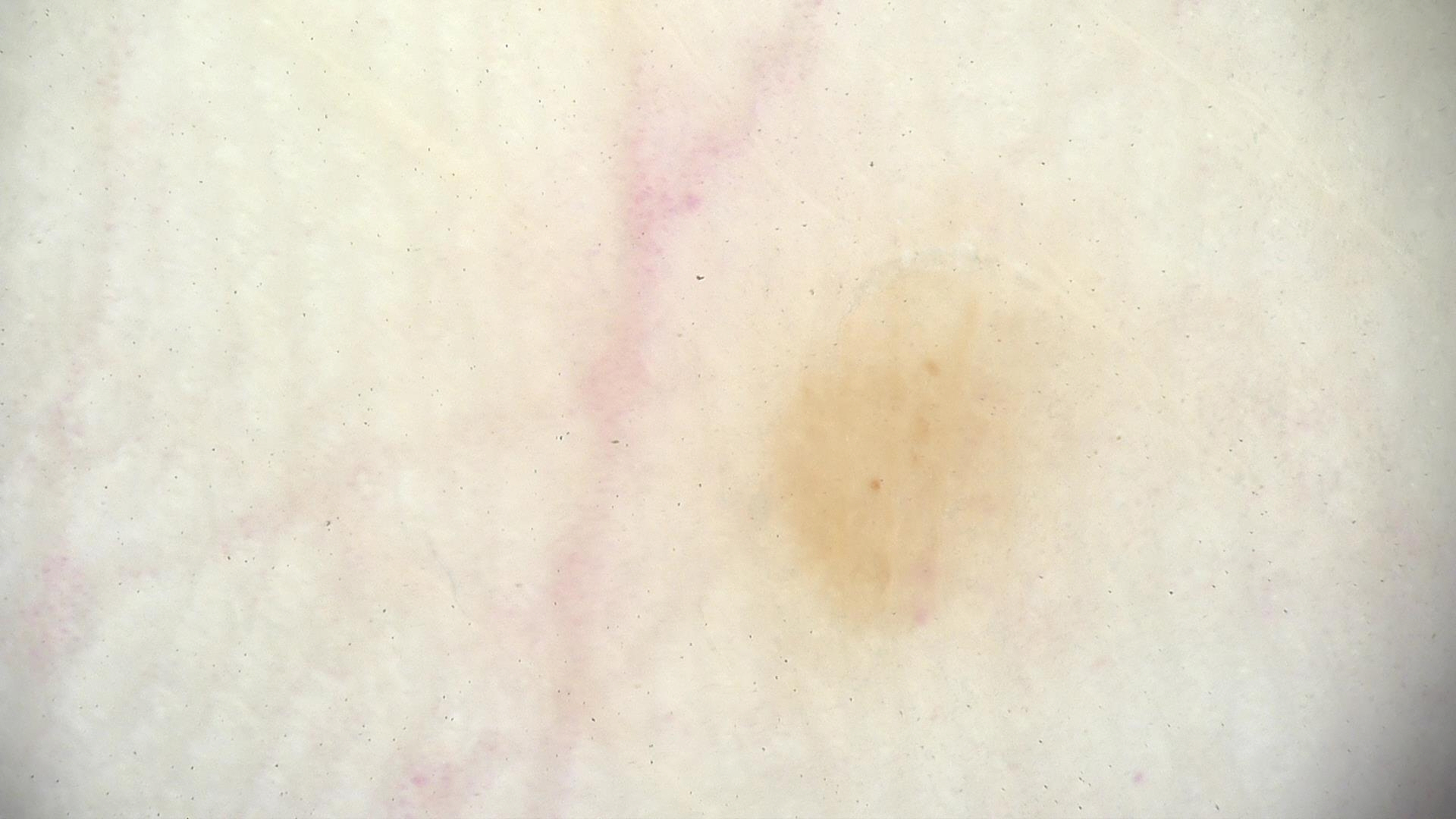A dermatoscopic image of a skin lesion.
The diagnosis was a benign lesion — an acral dysplastic junctional nevus.